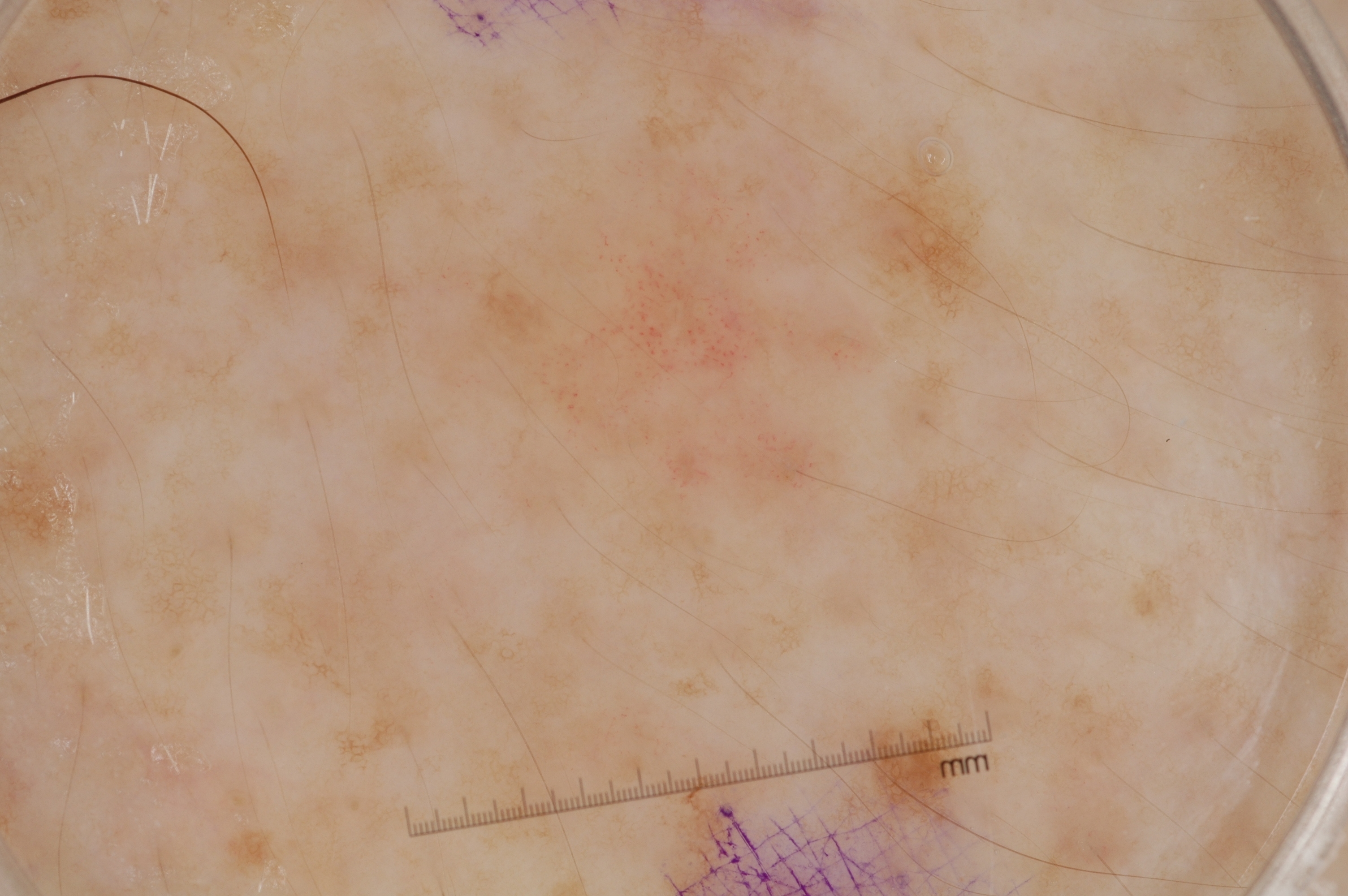imaging = dermoscopy of a skin lesion; subject = male, aged approximately 45; dermoscopic features assessed but absent = milia-like cysts, pigment network, streaks, and negative network; lesion location = [432, 112, 1010, 553]; assessment = a seborrheic keratosis.